The arm is involved · this image was taken at an angle · the patient is male: 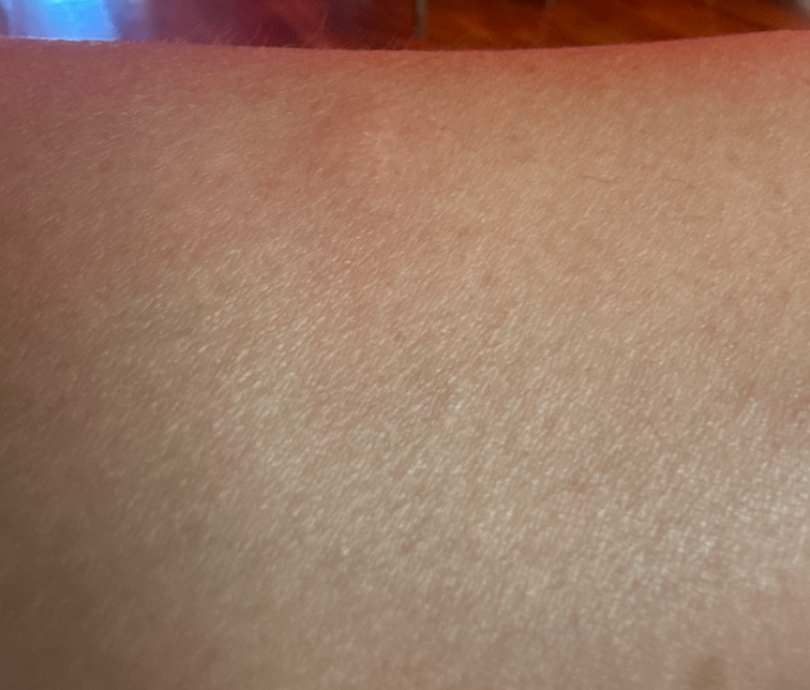Q: How does the patient describe it?
A: a rash
Q: What symptoms does the patient report?
A: itching and bothersome appearance
Q: Constitutional symptoms?
A: none reported
Q: Duration?
A: about one day
Q: What conditions are considered?
A: Urticaria (possible); Insect Bite (possible); Cyst (possible)